A skin lesion imaged with a dermatoscope. The subject is a male roughly 70 years of age.
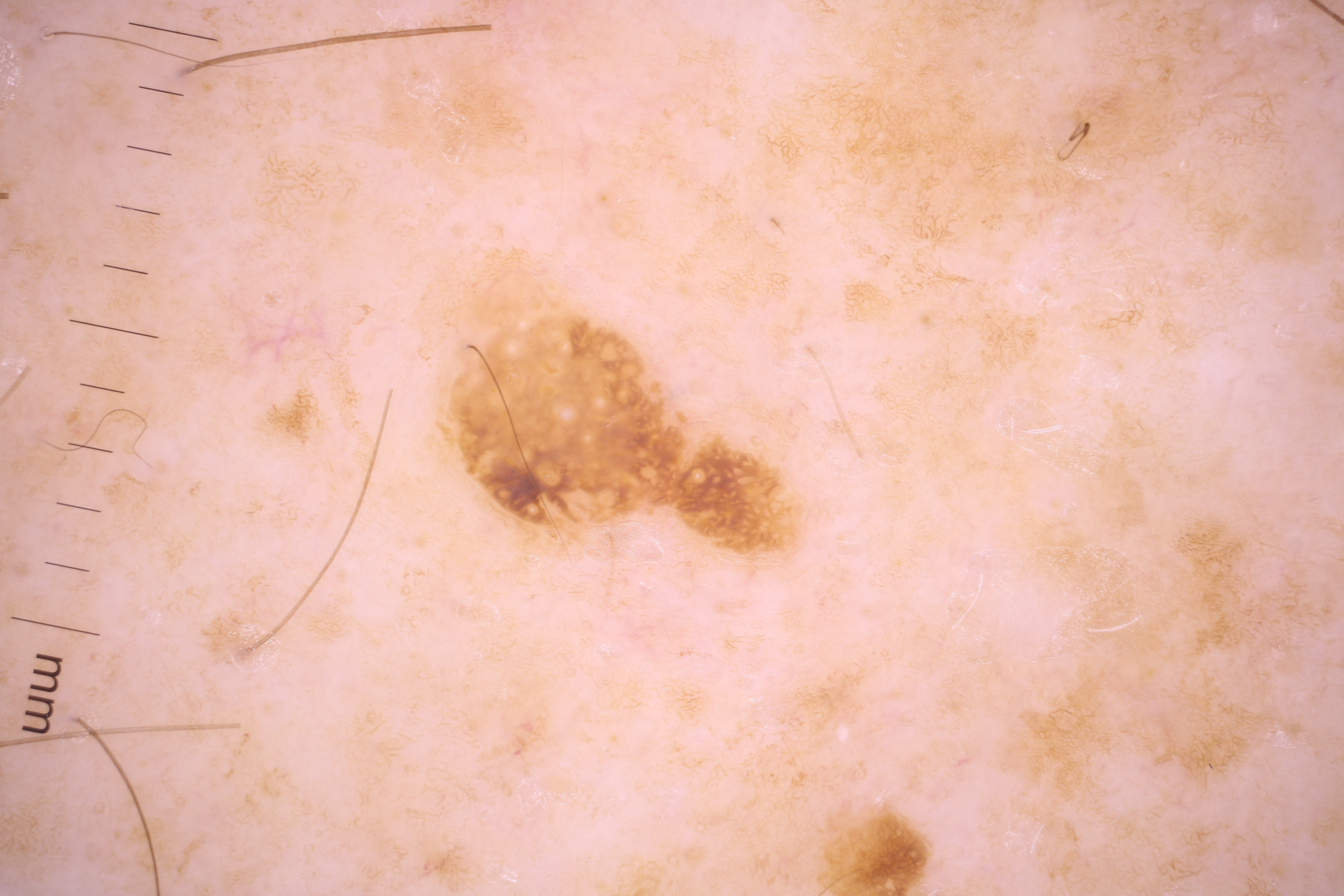Findings:
The lesion is located at x1=435, y1=247, x2=805, y2=564. A small lesion occupying a minor part of the field. Dermoscopically, the lesion shows milia-like cysts.
Impression:
Diagnosed as a seborrheic keratosis, a keratinocytic lesion.